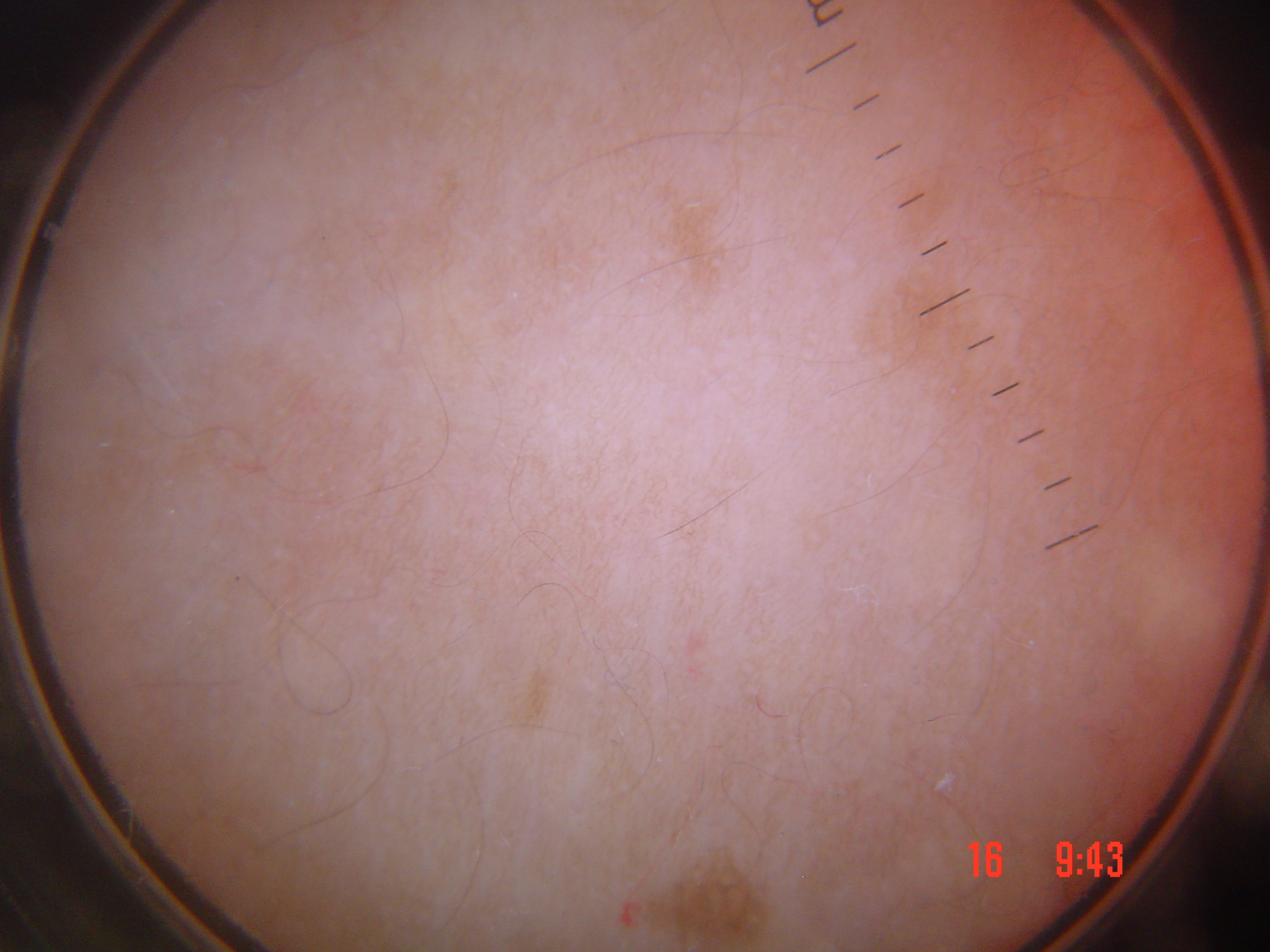diagnosis:
  name: lentigo simplex
  code: ls
  malignancy: benign
  super_class: melanocytic
  confirmation: expert consensus